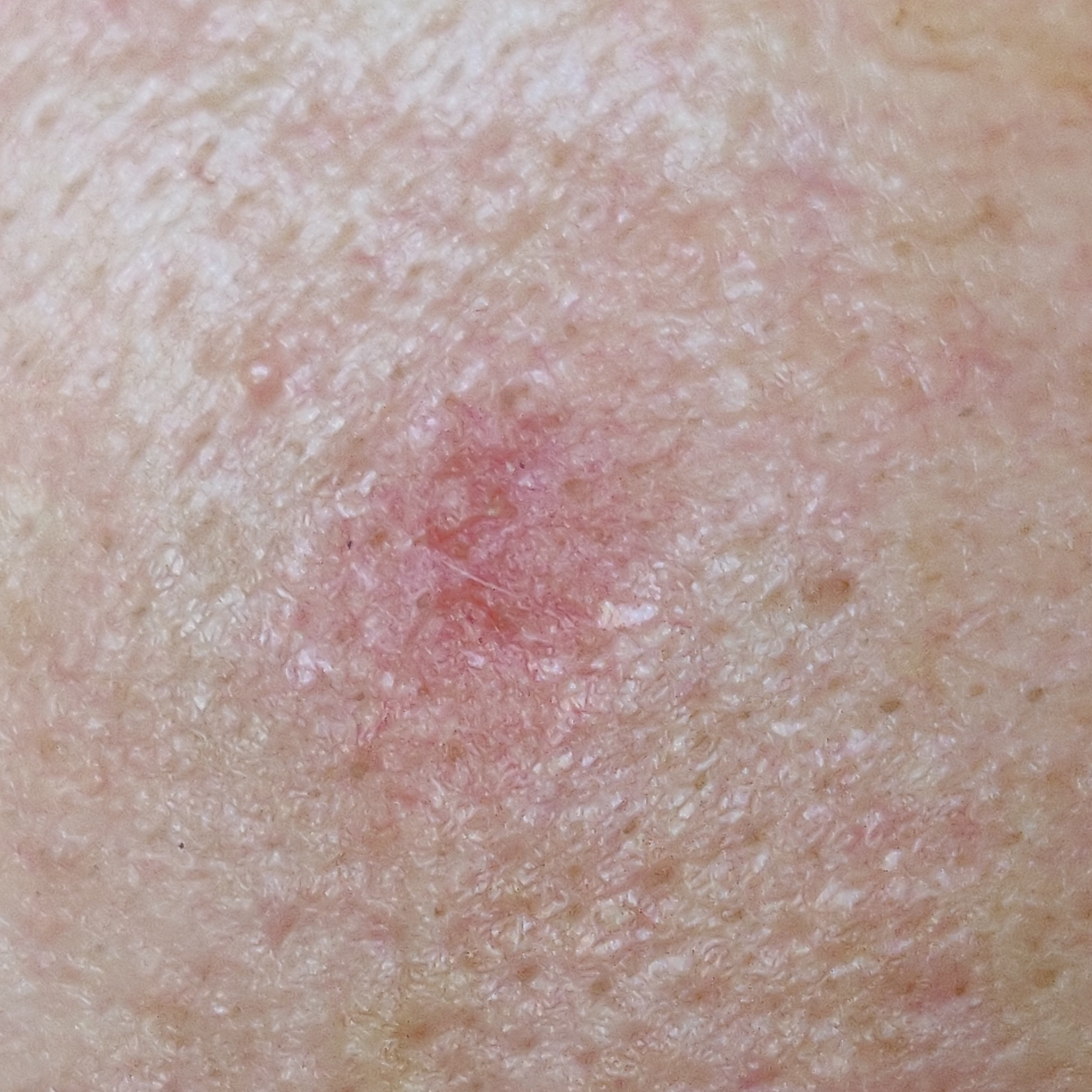A smartphone photograph of a skin lesion.
The lesion was found on the face.
The patient describes that the lesion itches.
Expert review favored a lesion with uncertain malignant potential — an actinic keratosis.